An image taken at an angle: 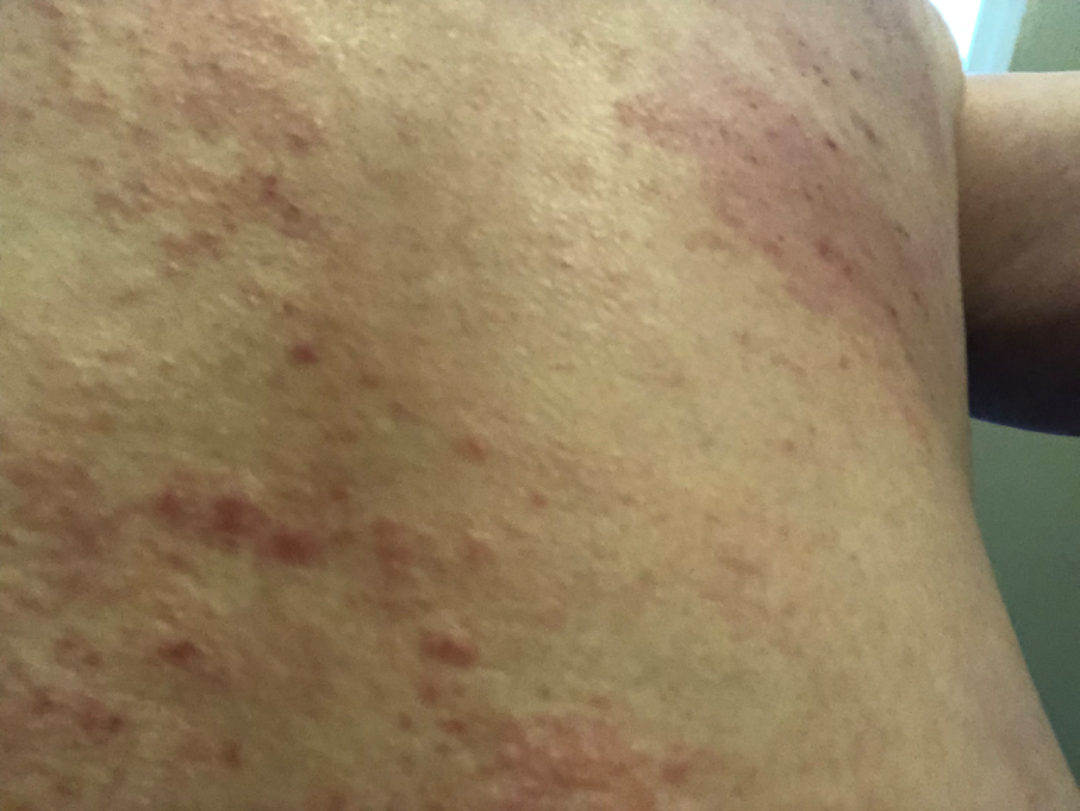On photographic review: most likely Grover's disease; an alternative is Acne; also consider Darier's disease.